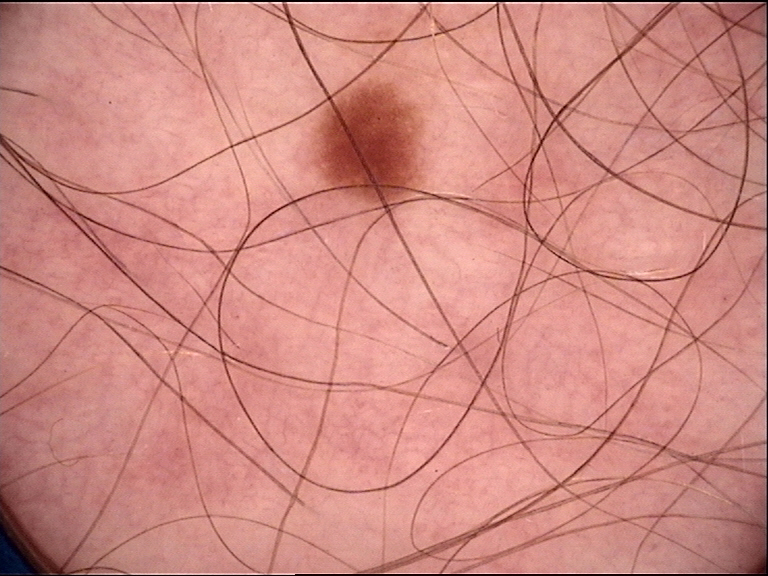<dermoscopy>
<image>dermatoscopy</image>
<diagnosis>
<name>dysplastic junctional nevus</name>
<code>jd</code>
<malignancy>benign</malignancy>
<super_class>melanocytic</super_class>
<confirmation>expert consensus</confirmation>
</diagnosis>
</dermoscopy>